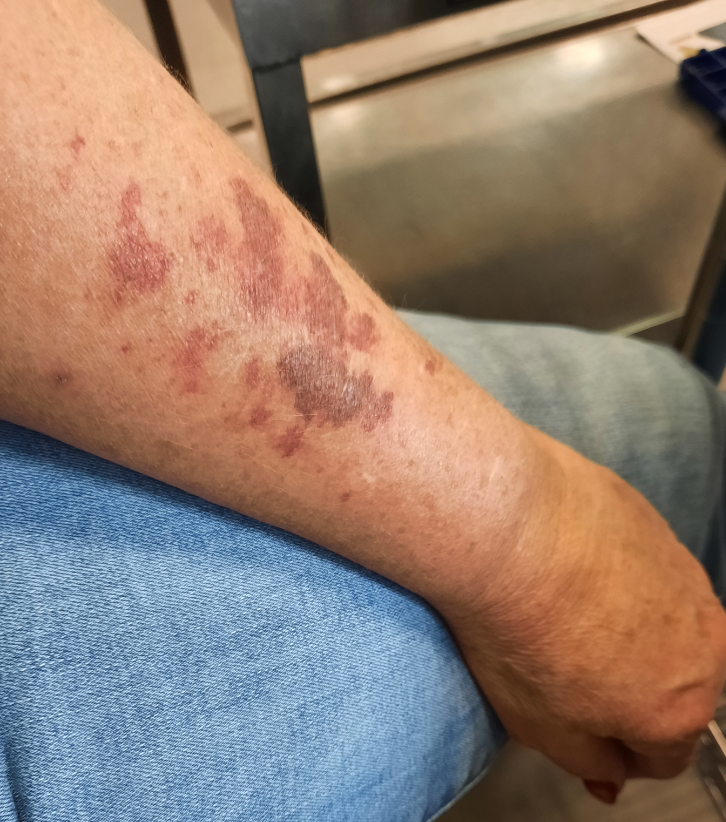shot type = at a distance
patient = female, age 50–59
site = arm
impression = favoring ecchymoses; with consideration of Kaposi's sarcoma of skin; also raised was Leukocytoclastic Vasculitis